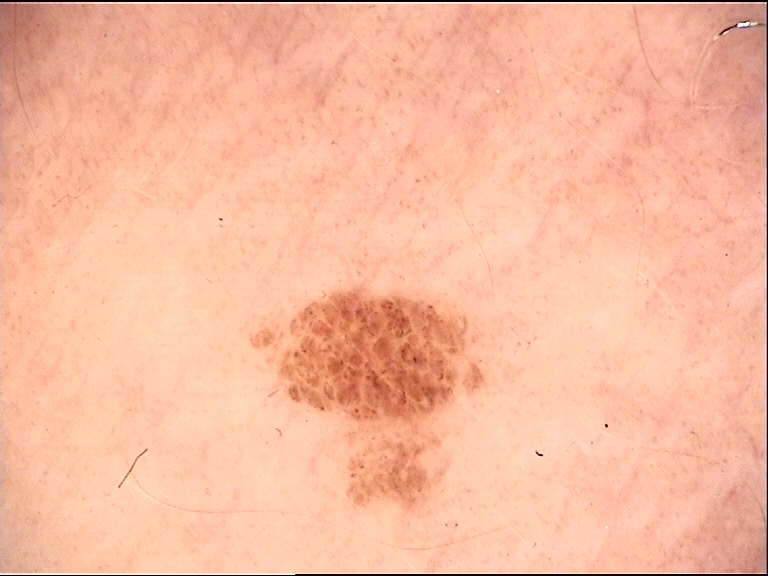<lesion>
  <image>dermatoscopy</image>
  <lesion_type>
    <main_class>banal</main_class>
    <pattern>junctional</pattern>
  </lesion_type>
  <diagnosis>
    <name>junctional nevus</name>
    <code>jb</code>
    <malignancy>benign</malignancy>
    <super_class>melanocytic</super_class>
    <confirmation>expert consensus</confirmation>
  </diagnosis>
</lesion>